Contact-polarized dermoscopy of a skin lesion; a male subject about 75 years old: 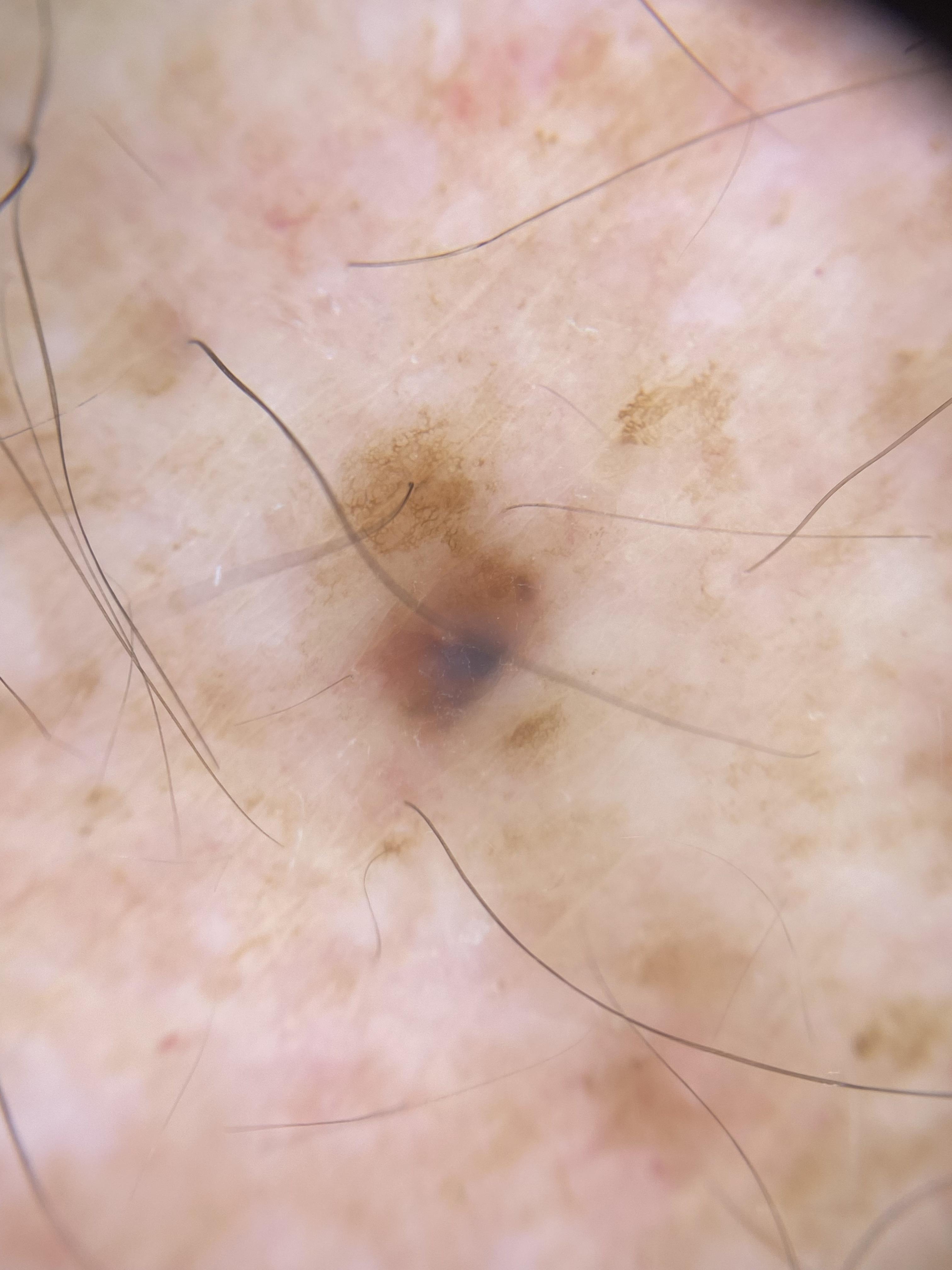The lesion was found on the trunk. The biopsy diagnosis was a benign, melanocytic lesion — a nevus.